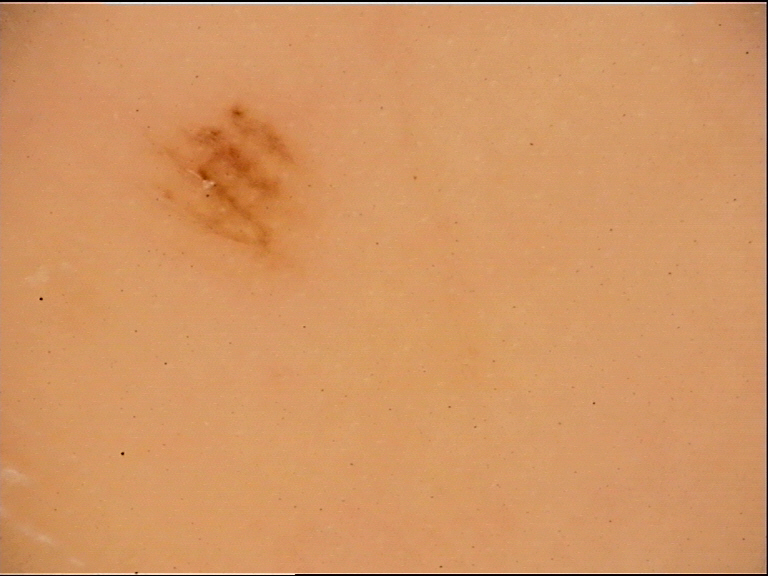– assessment · acral junctional nevus (expert consensus)